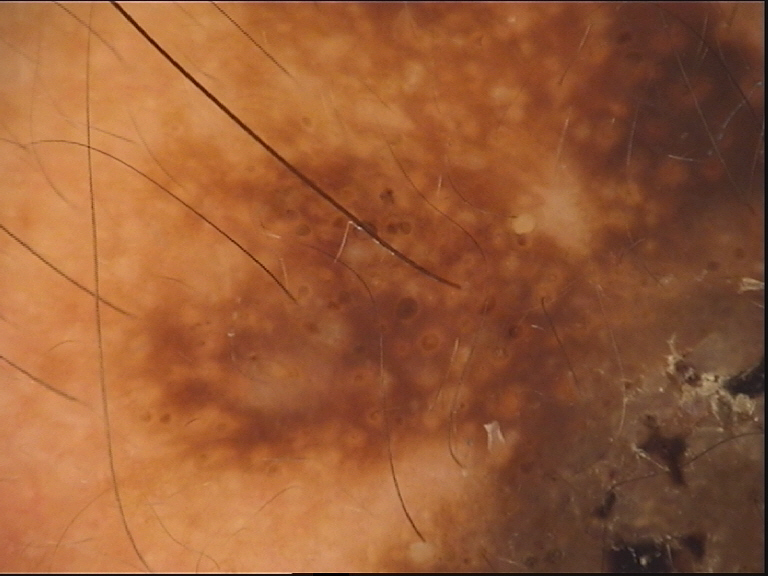Conclusion: The diagnostic label was a seborrheic keratosis.